Dermoscopy of a skin lesion.
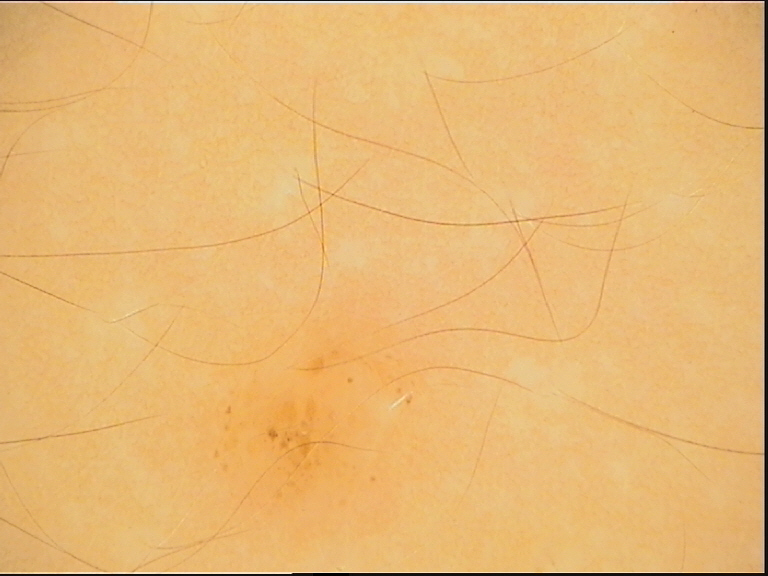Q: What was the diagnostic impression?
A: junctional nevus (expert consensus)